A dermoscopy image of a single skin lesion.
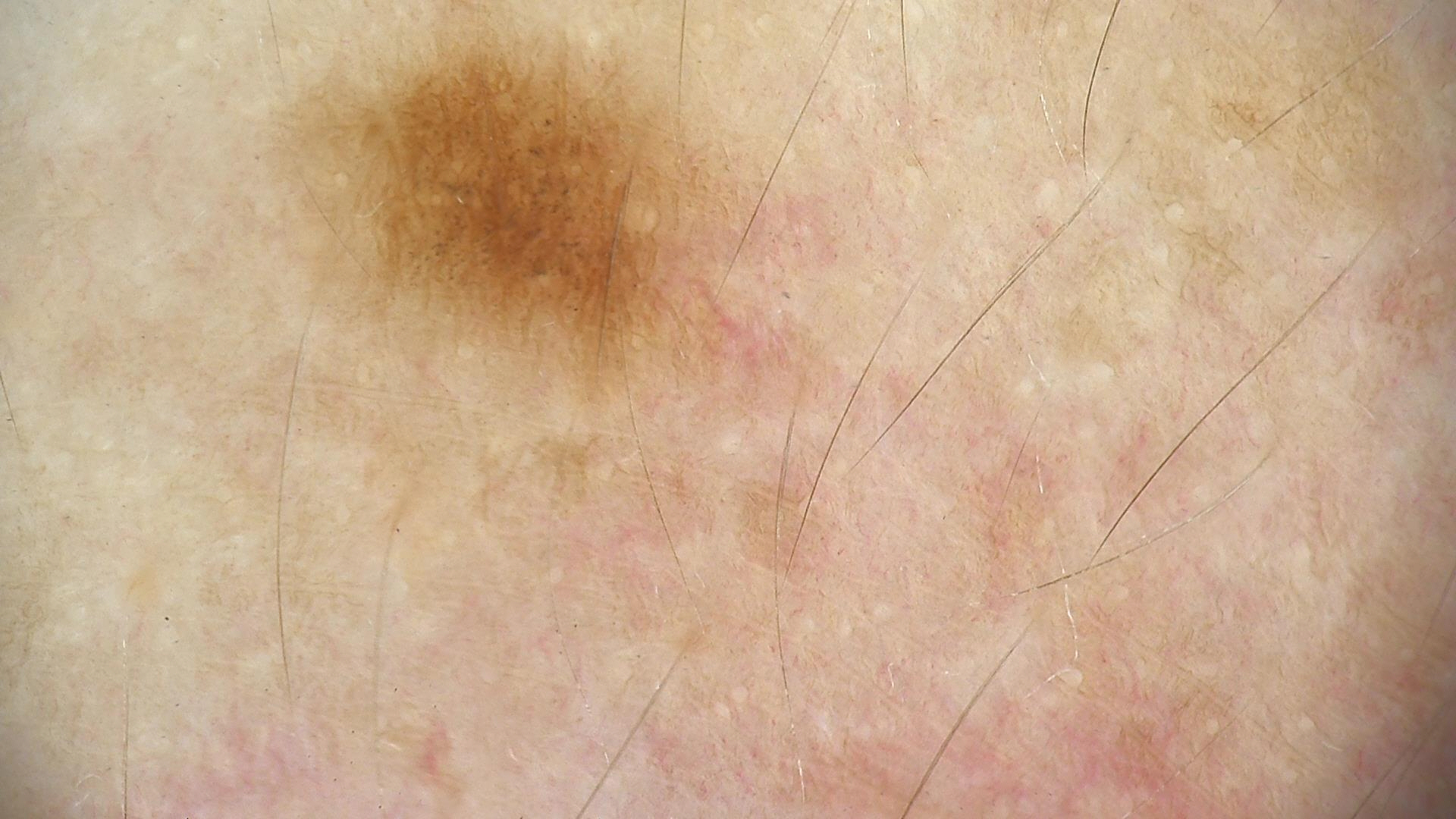Diagnosed as a dysplastic junctional nevus.